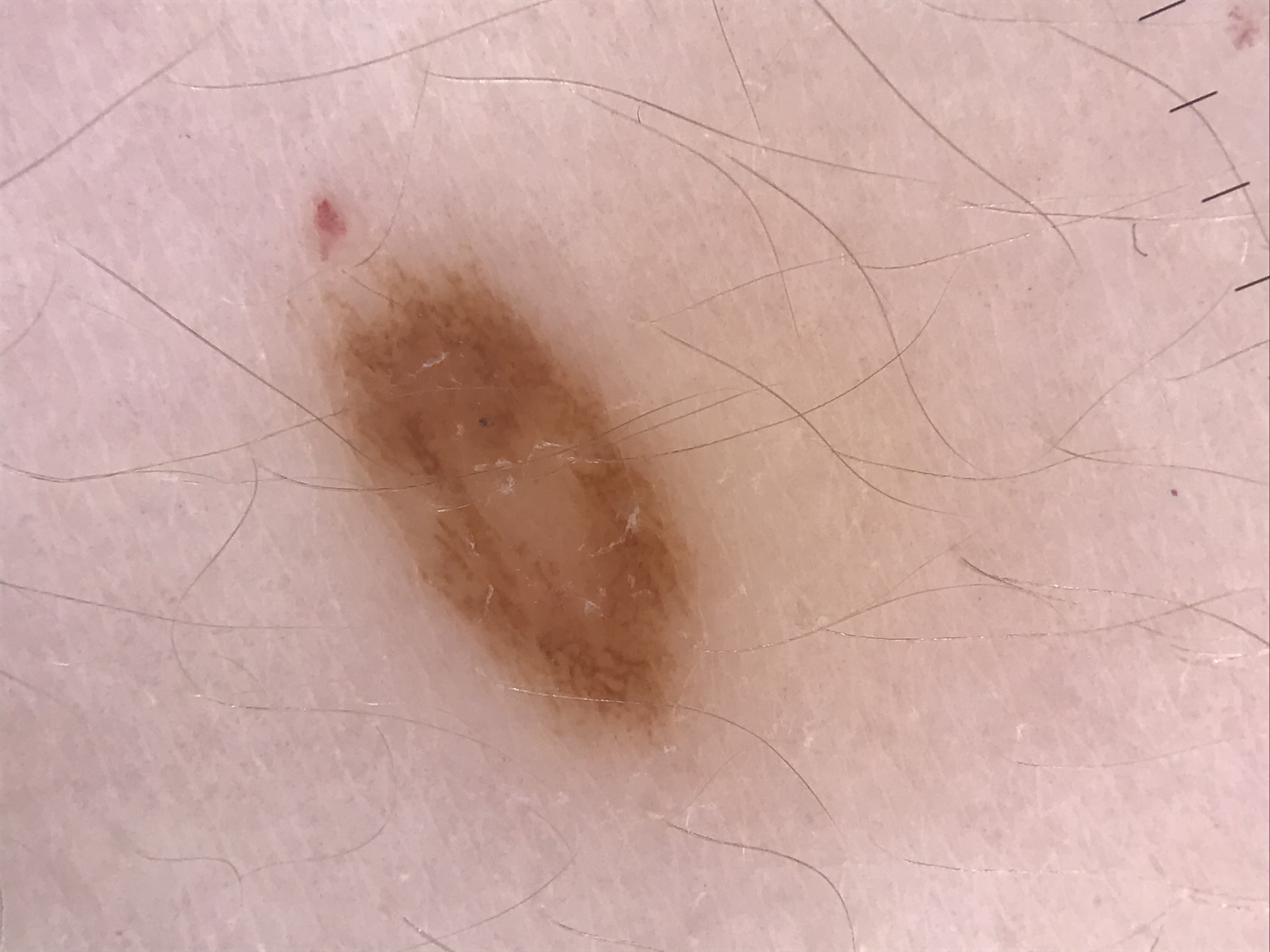Impression:
Labeled as a dysplastic compound nevus.